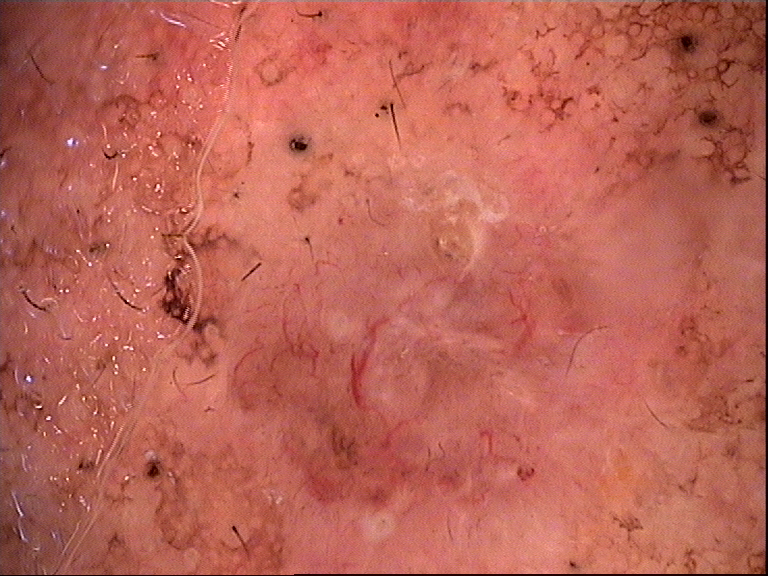Findings: The architecture is that of a keratinocytic lesion. Conclusion: Histopathologically confirmed as a basal cell carcinoma.